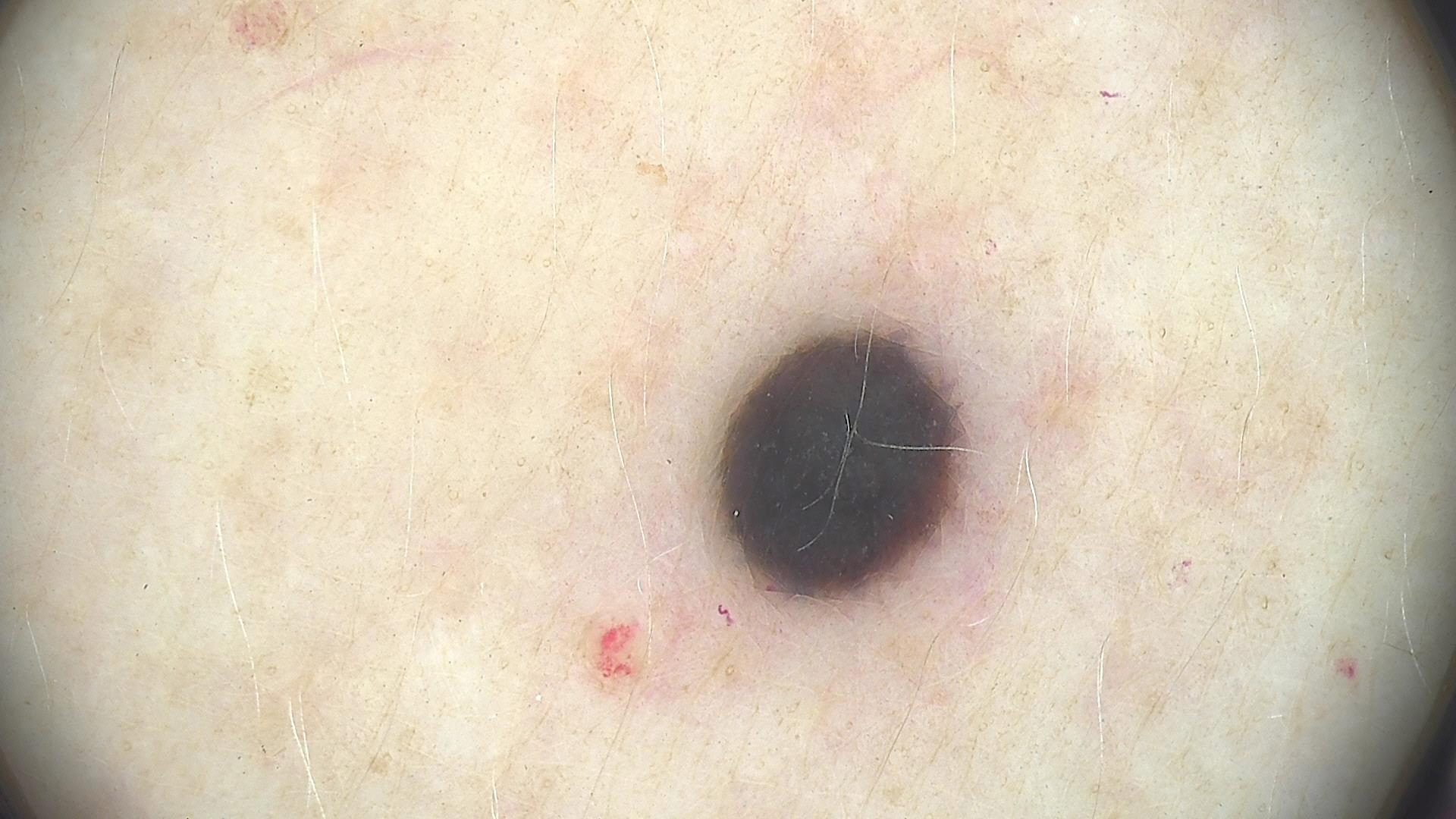A dermoscopic image of a skin lesion. This is a banal, dermal lesion. Diagnosed as a blue nevus.